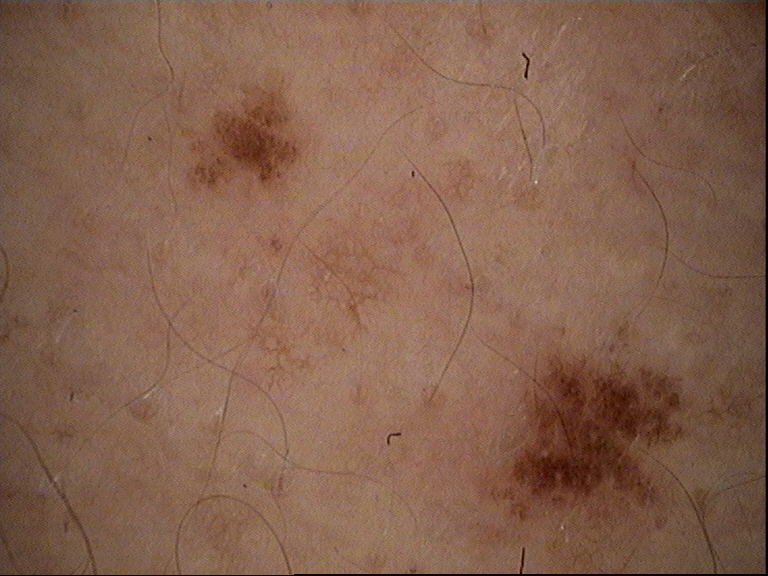Impression: Diagnosed as a benign lesion — a dysplastic junctional nevus.